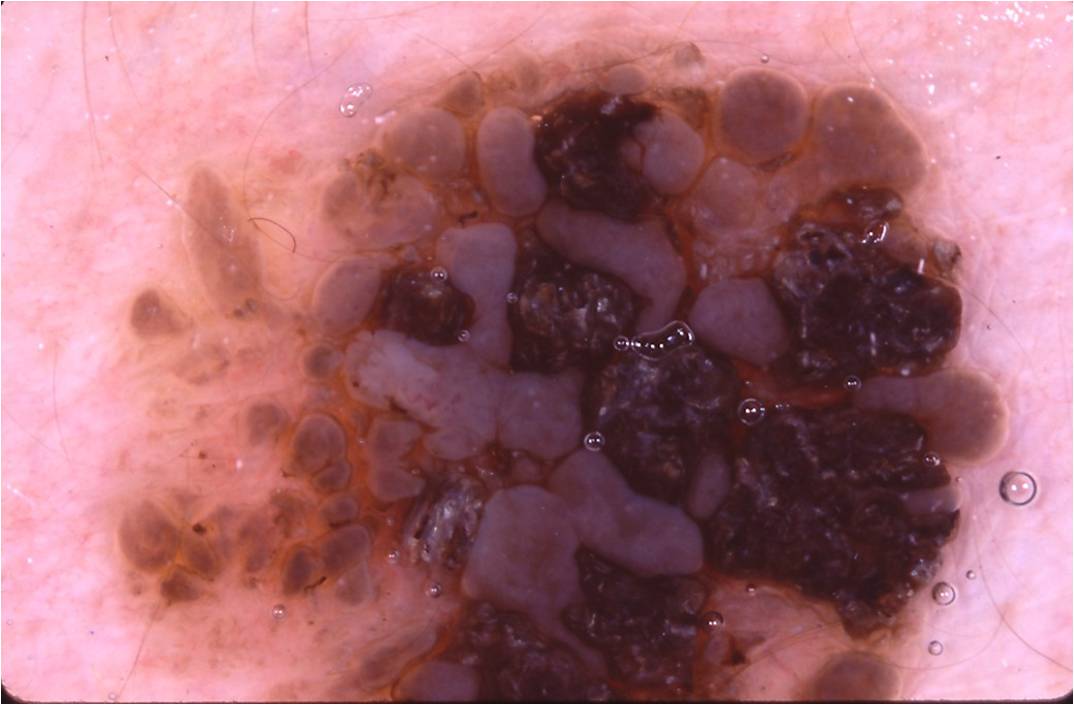Case summary:
A dermatoscopic image of a skin lesion. In (x1, y1, x2, y2) order, the lesion is located at 87 17 1022 701.
Conclusion:
The clinical diagnosis was a benign skin lesion.